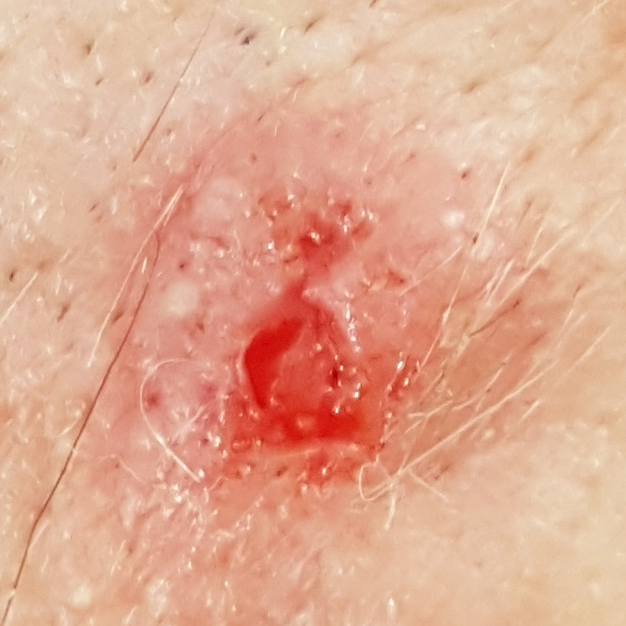Clinical context:
A male subject in their late 30s. A smartphone photograph of a skin lesion. The lesion is on the face. Per patient report, the lesion hurts, itches, is elevated, has bled, and has grown, but has not changed.
Conclusion:
The biopsy diagnosis was a basal cell carcinoma.